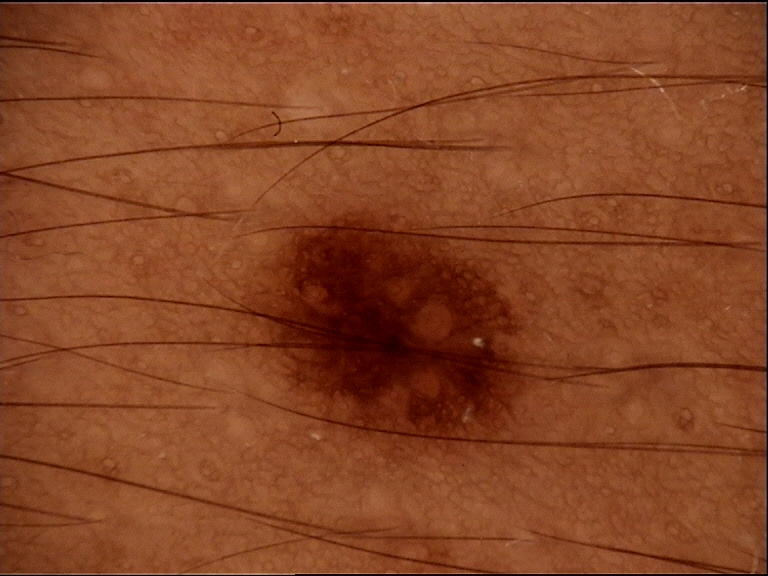image: dermoscopy
diagnosis:
  name: dysplastic junctional nevus
  code: jd
  malignancy: benign
  super_class: melanocytic
  confirmation: expert consensus